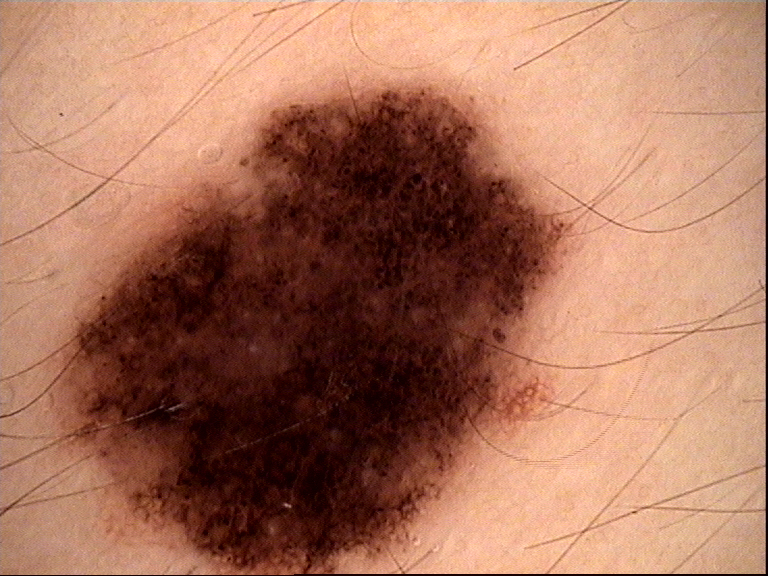* diagnostic label — dysplastic compound nevus (expert consensus)